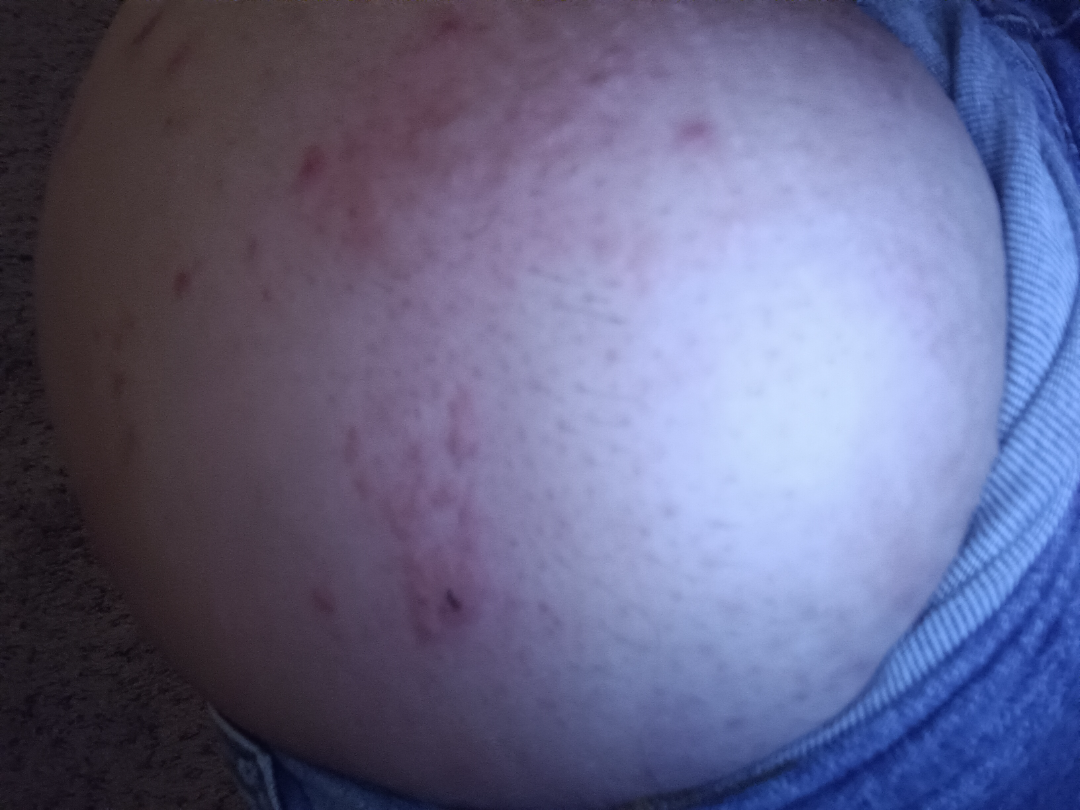Q: Could the case be diagnosed?
A: unable to determine